A female patient about 25 years old · a dermoscopic image of a skin lesion — 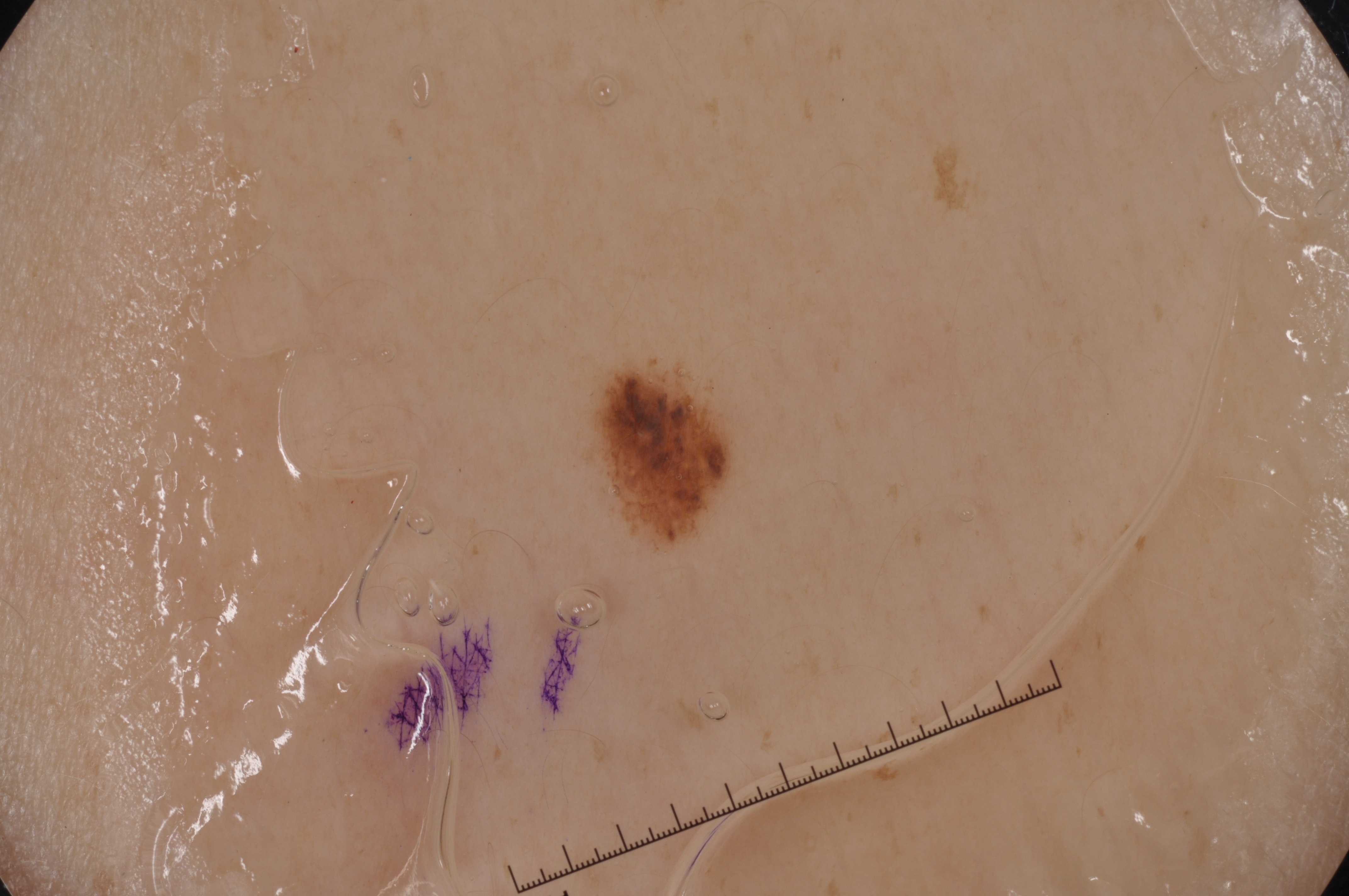Summary: In (x1, y1, x2, y2) order, the lesion spans [601, 371, 727, 518]. The lesion is small relative to the field of view. Dermoscopic review identifies no streaks, milia-like cysts, pigment network, or negative network. Conclusion: Consistent with a melanocytic nevus.